Symptoms reported: burning, bothersome appearance, pain and enlargement · the contributor is 60–69, male · texture is reported as fluid-filled, rough or flaky and raised or bumpy · the affected area is the arm · the patient also reports joint pain · the condition has been present for one to four weeks · the photo was captured at a distance · skin tone: FST II; lay graders estimated Monk skin tone scale 1 or 2 (two reviewer pools).
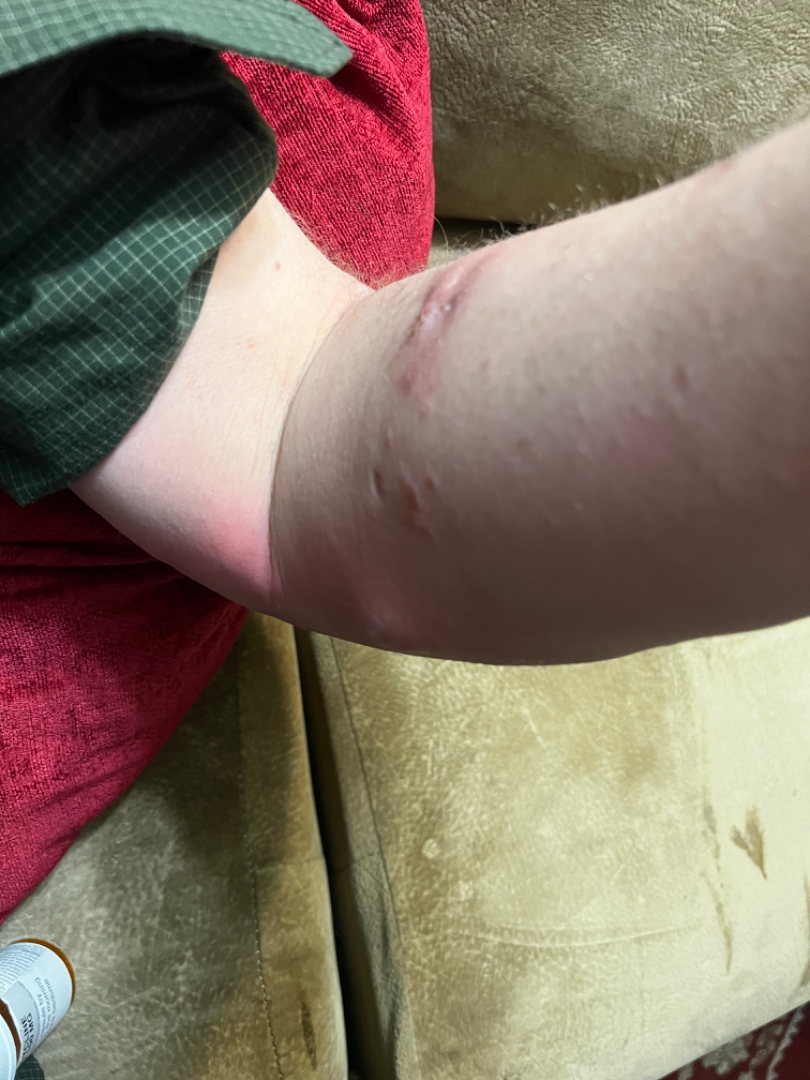Assessment: On photographic review, favoring Abscess; also consider Cellulitis; less likely is Localised skin eruption due to drugs and medicaments; lower on the differential is Lymphocutaneous sporotrichosis; less probable is Cutaneous leishmaniasis.